A dermatoscopic image of a skin lesion: 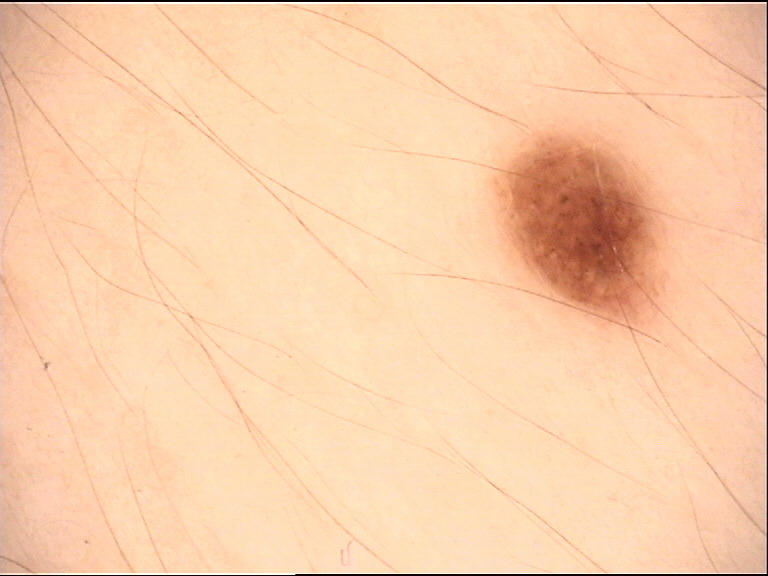Conclusion:
Diagnosed as a benign lesion — a dysplastic compound nevus.